The subject is a male roughly 65 years of age. A dermoscopic close-up of a skin lesion:
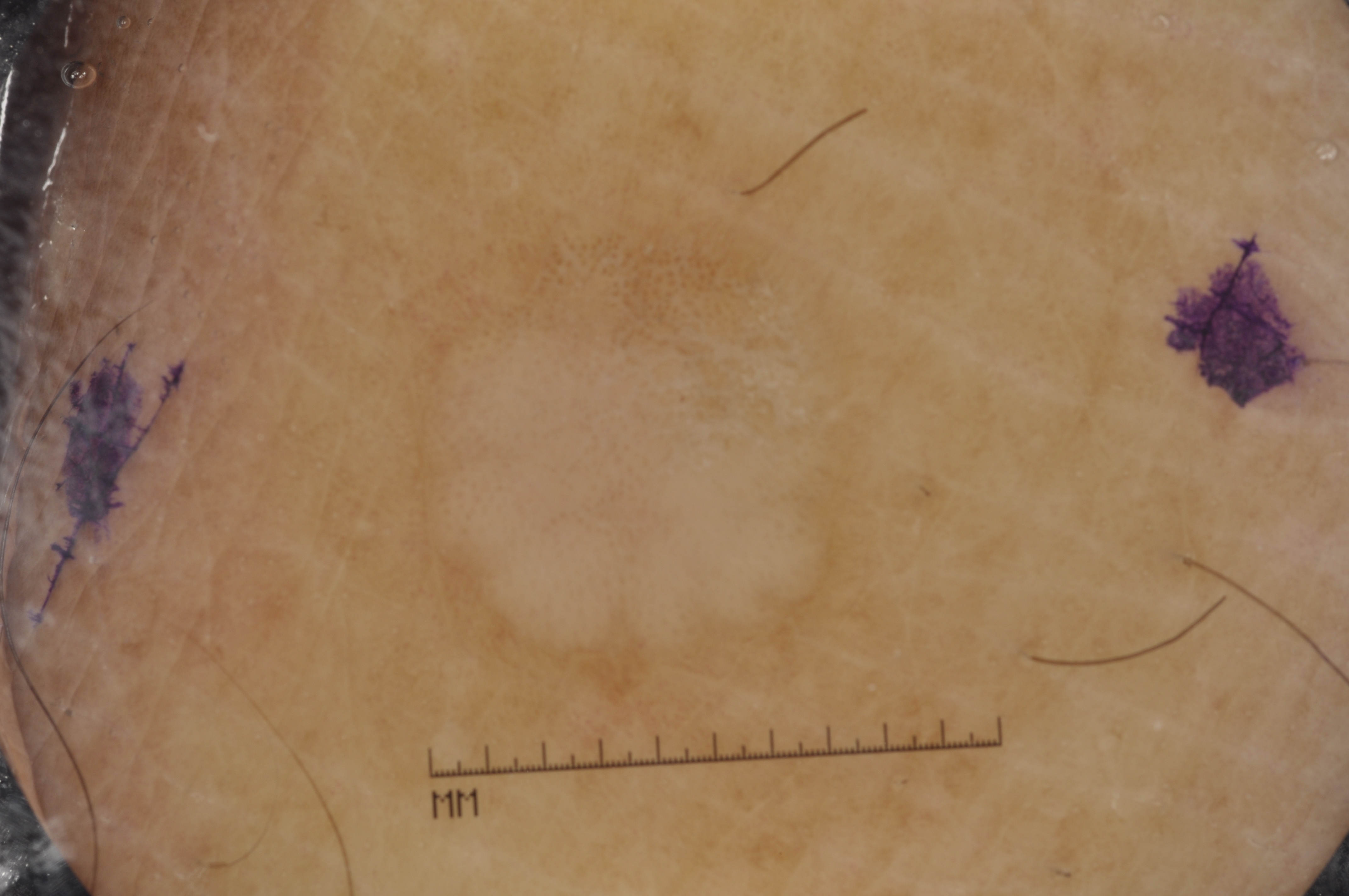dermoscopic_features:
  present: []
  absent:
    - pigment network
    - negative network
    - milia-like cysts
    - streaks
lesion_location:
  bbox_xyxy:
    - 395
    - 216
    - 931
    - 727
diagnosis:
  name: seborrheic keratosis
  malignancy: benign
  lineage: keratinocytic
  provenance: clinical